A skin lesion imaged with a dermatoscope: 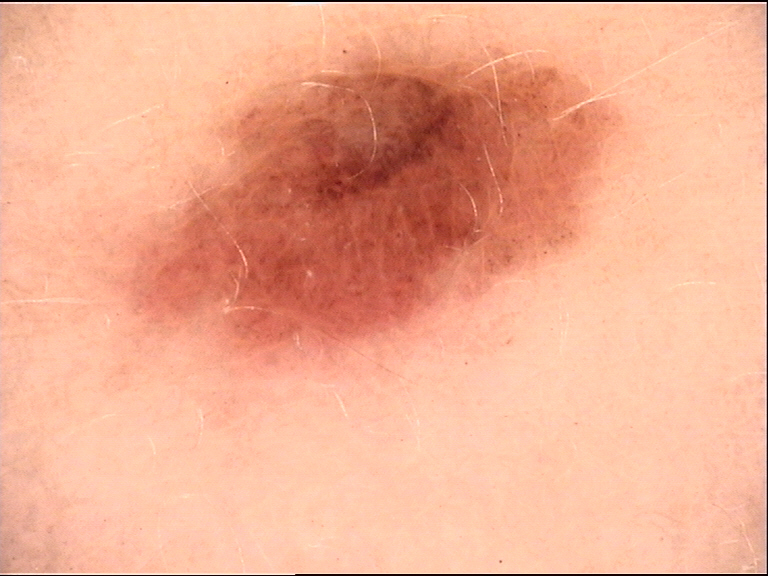Conclusion: The diagnostic label was a dysplastic junctional nevus.